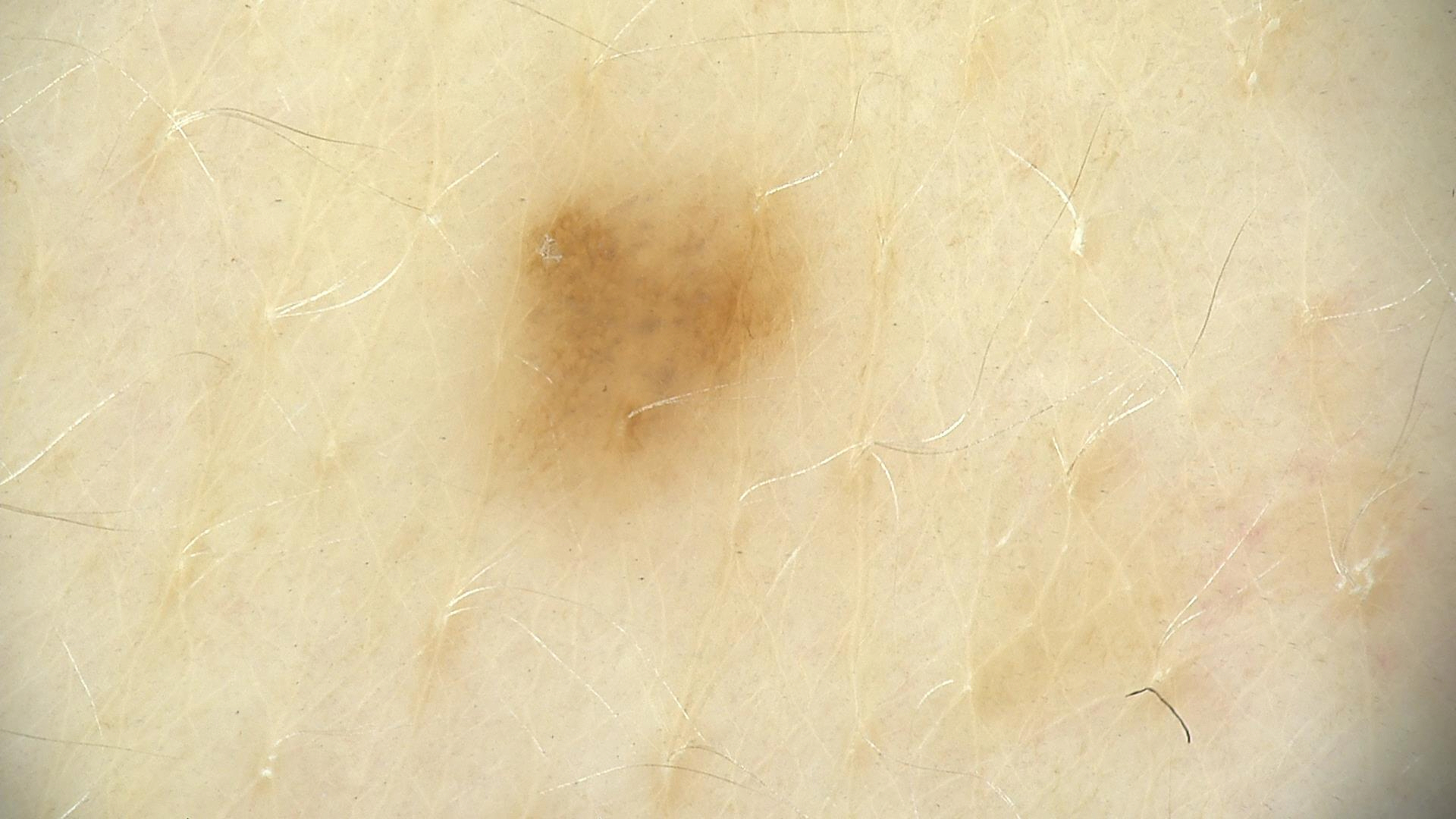Findings:
* label — dysplastic junctional nevus (expert consensus)